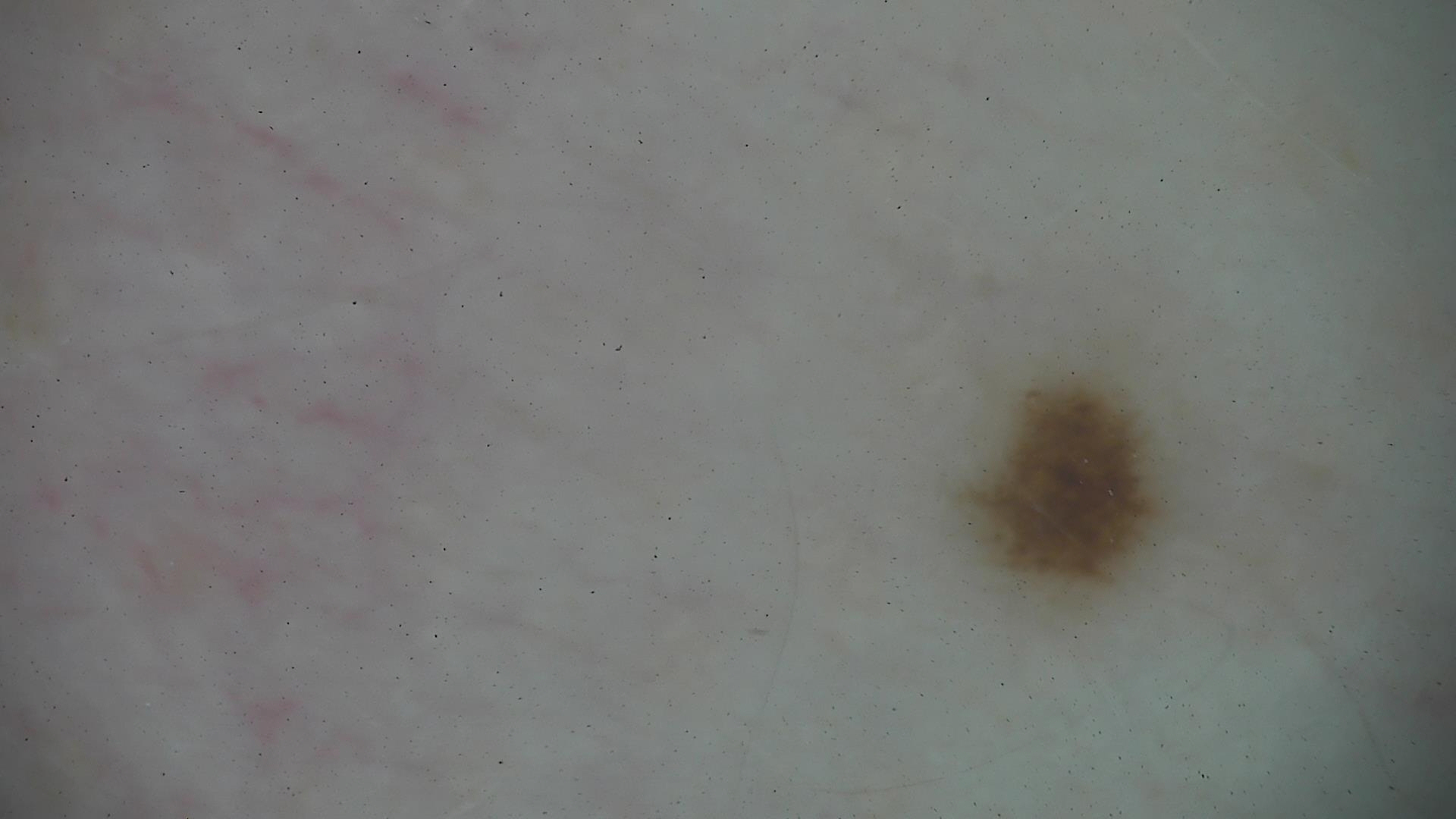image type = dermatoscopy
label = dysplastic junctional nevus (expert consensus)